This image was taken at an angle · the affected area is the arm:
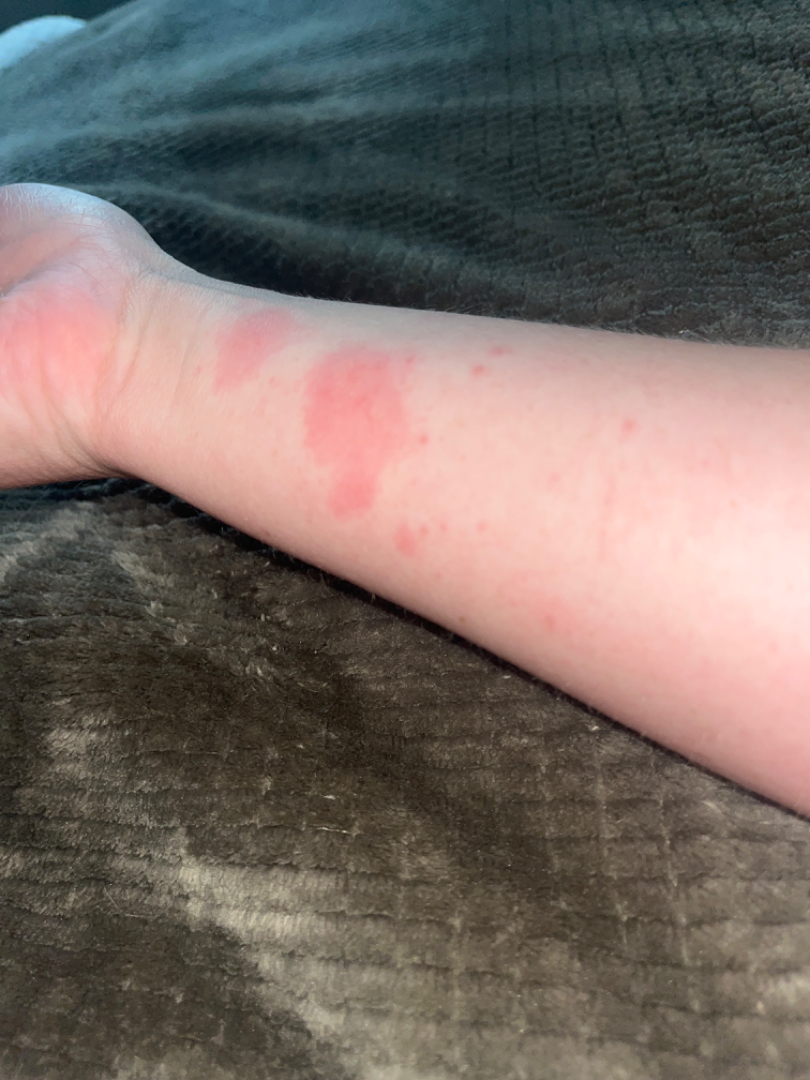Reported duration is less than one week.
On photographic review by a dermatologist, Insect Bite (leading); Urticaria (considered); Allergic Contact Dermatitis (less likely).